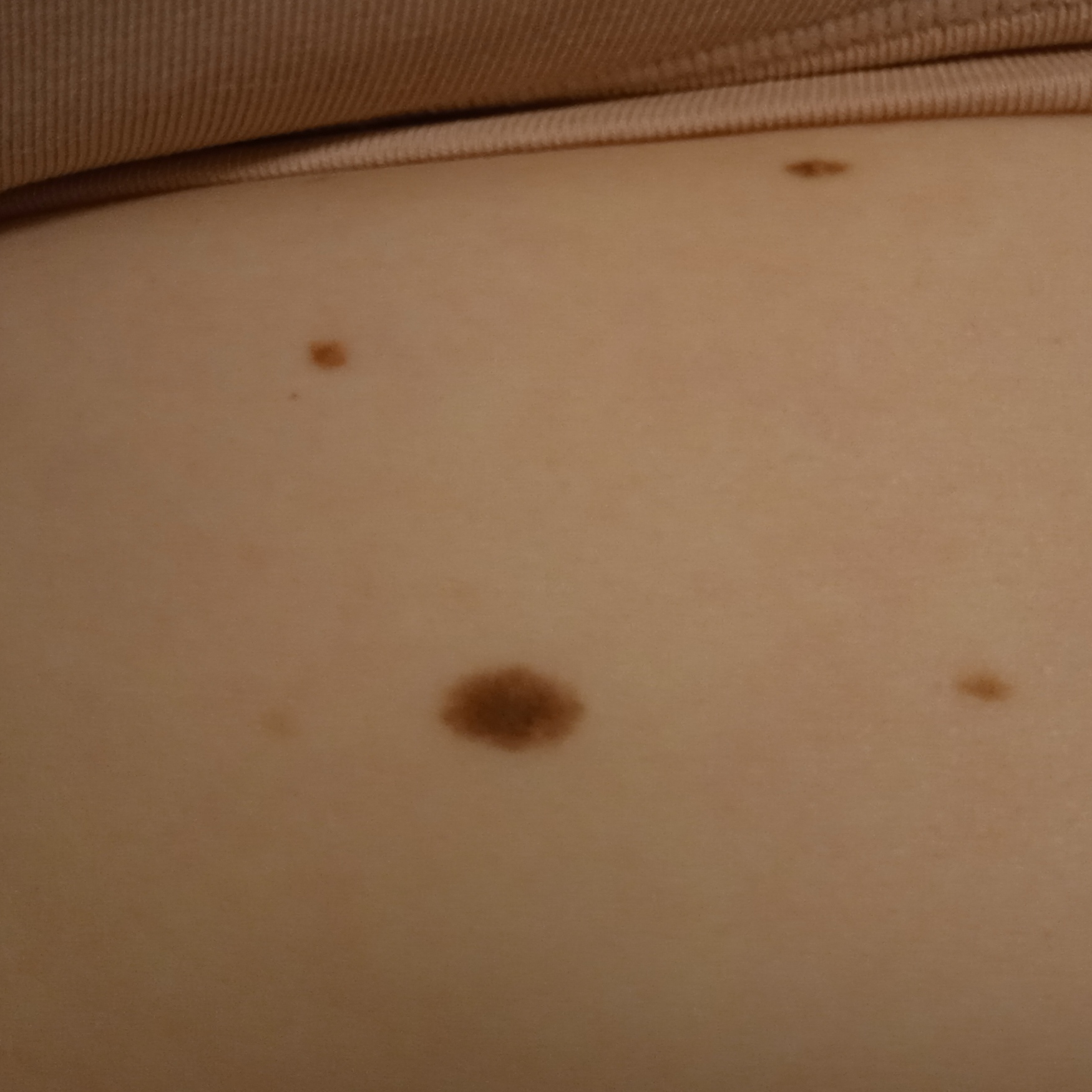| field | value |
|---|---|
| diagnostic label | melanocytic nevus (dermatologist consensus) |